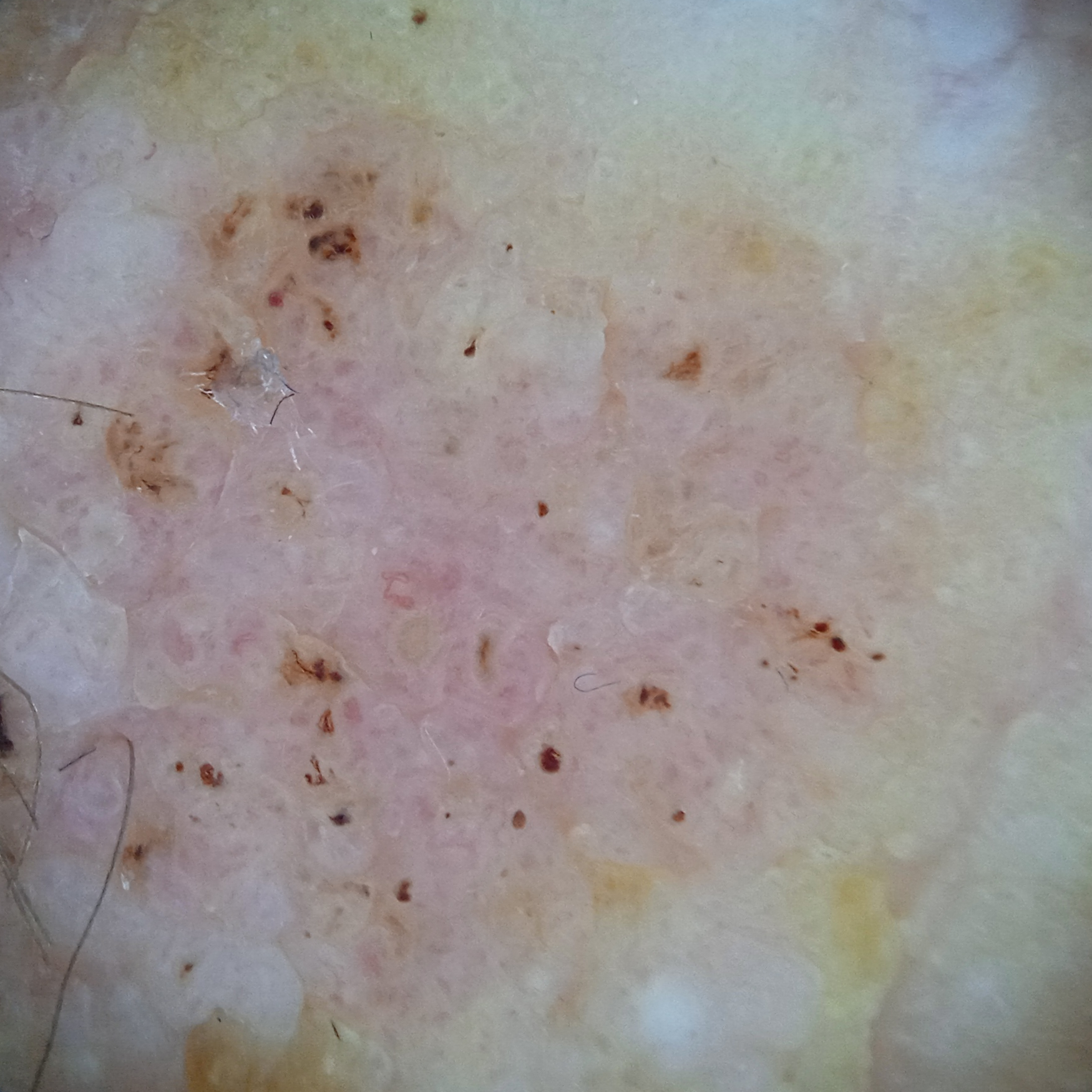Assessment:
The diagnostic impression was a seborrheic keratosis.